Present for one to four weeks · female subject, age 30–39 · the lesion is associated with darkening, pain, itching, burning and bothersome appearance · this is a close-up image · located on the back of the hand · no constitutional symptoms were reported.
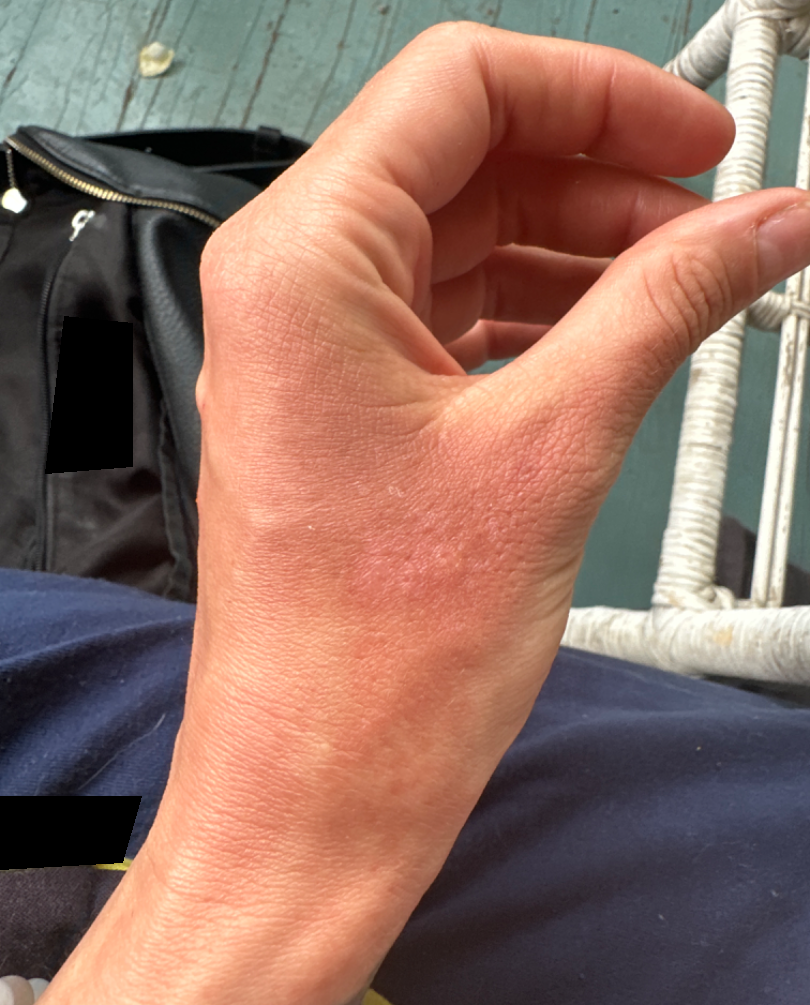diagnostic considerations = the leading impression is Irritant Contact Dermatitis; also consider Allergic Contact Dermatitis.